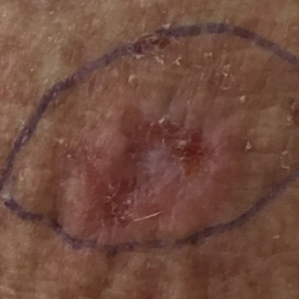Notes:
* risk factors: prior skin cancer (patient or family), pesticide exposure, prior malignancy (patient or family)
* subject: female, 69 years old
* image: clinical photo
* Fitzpatrick: II
* location: a forearm
* lesion diameter: 13 × 9 mm
* symptoms: itching
* diagnostic label: actinic keratosis (biopsy-proven)